A male subject age 67. The patient was assessed as FST II.
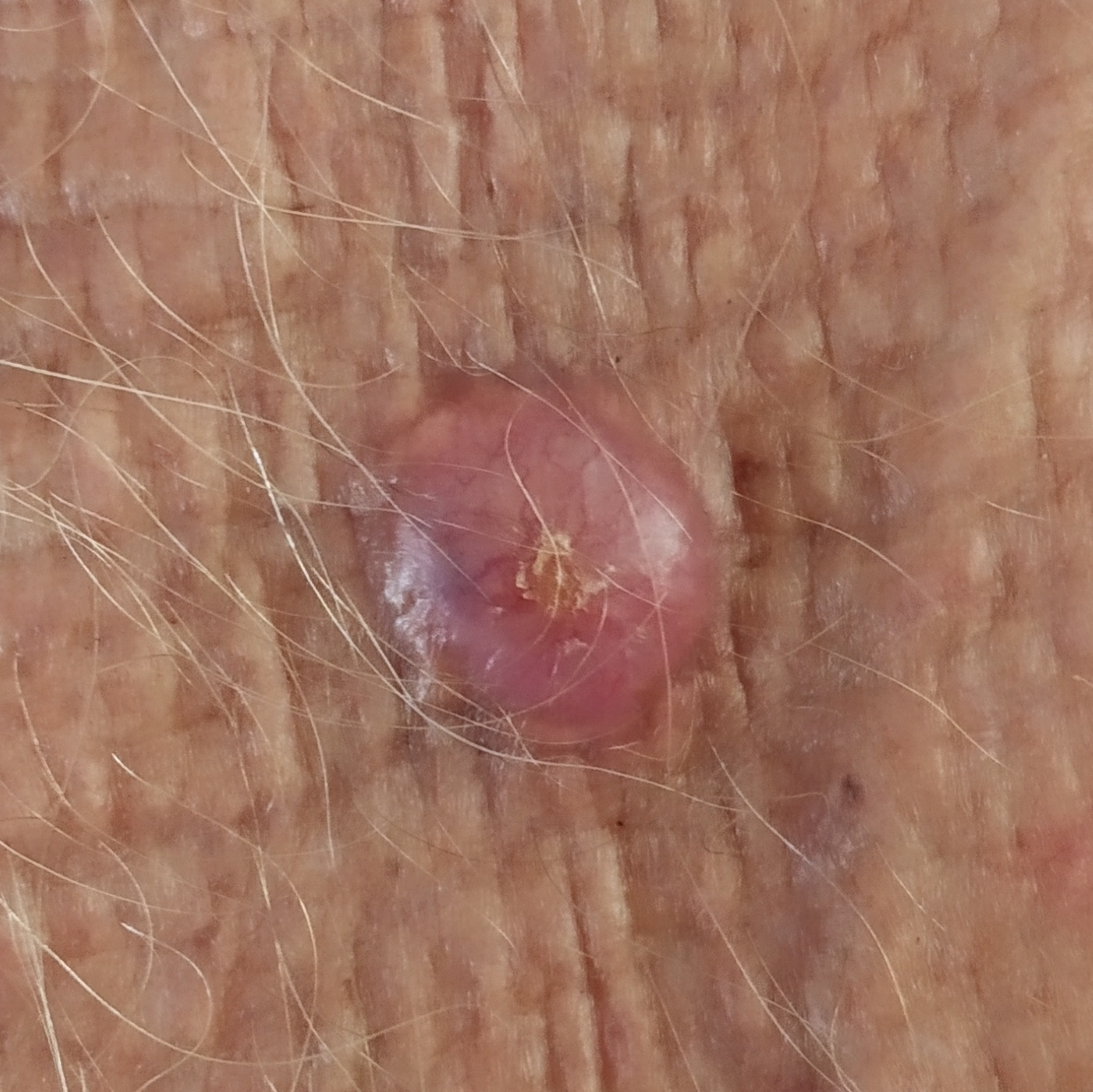Located on a forearm.
The lesion is roughly 21 by 13 mm.
By the patient's account, the lesion is elevated and itches, but has not bled.
Confirmed on histopathology as a basal cell carcinoma.